A skin lesion imaged with contact-polarized dermoscopy. The chart notes melanoma in a first-degree relative. Fitzpatrick skin type III — 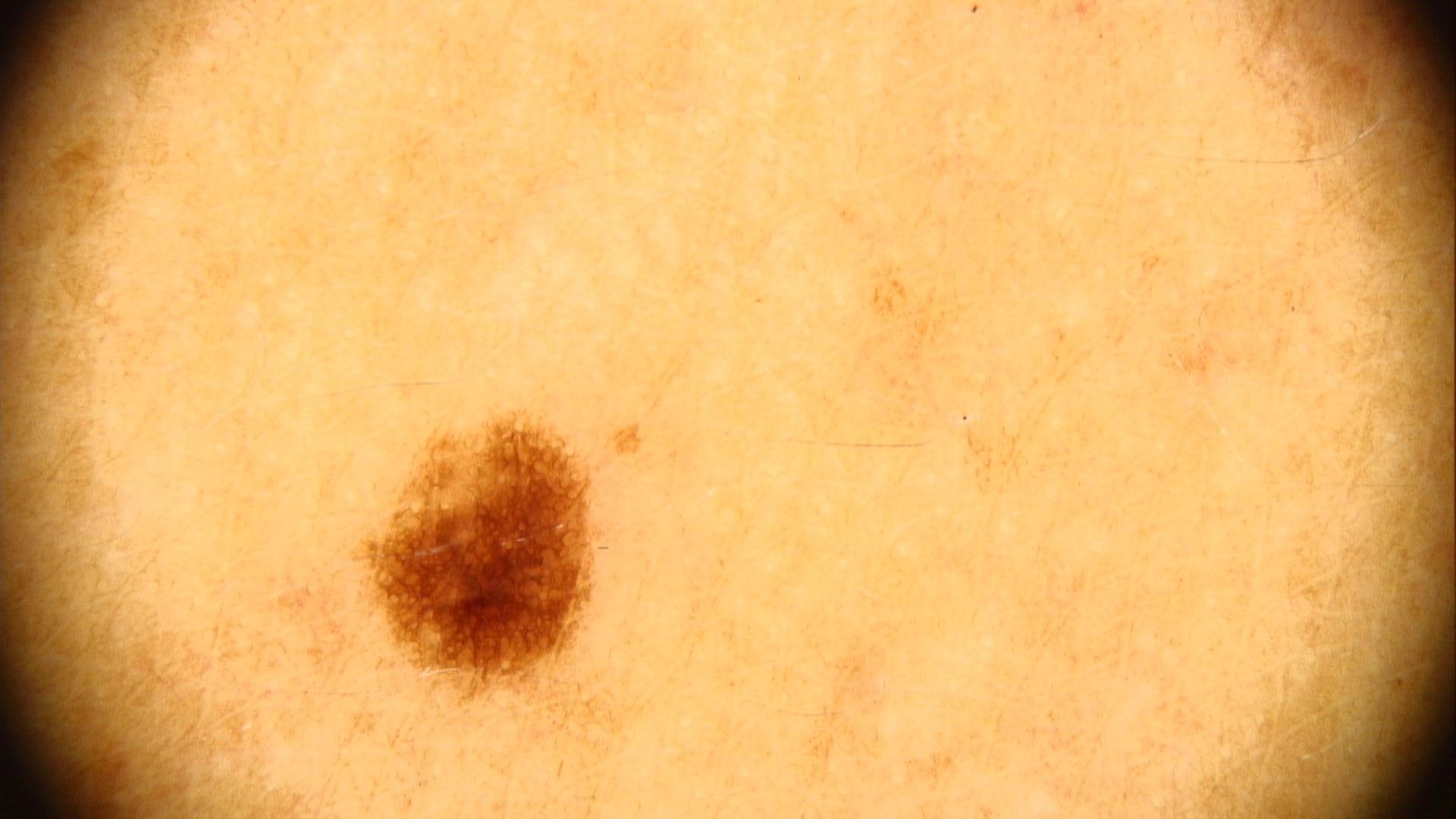Q: Where is the lesion located?
A: the trunk
Q: What was the clinical impression?
A: Nevus